The subject is a female aged 40–49, the lesion involves the arm, the photograph was taken at an angle: 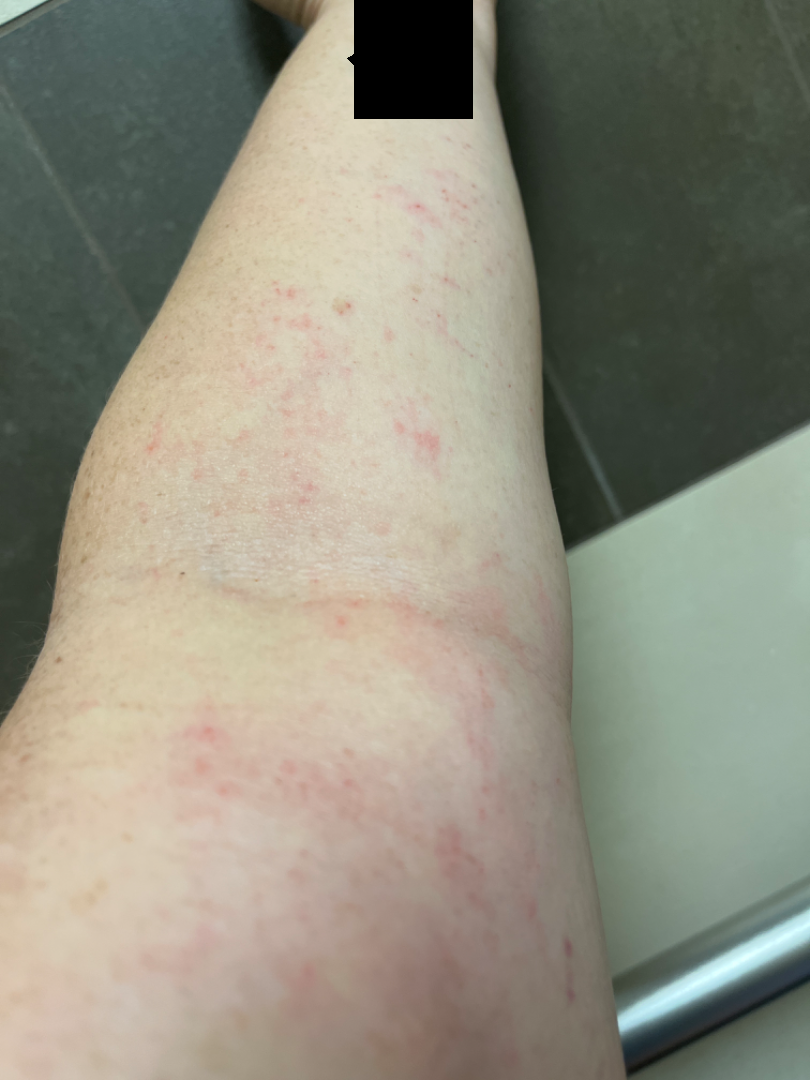systemic symptoms — none reported | patient-reported symptoms — itching, bothersome appearance and burning | self-categorized as — skin that appeared healthy to them | history — less than one week | texture — raised or bumpy | dermatologist impression — Acute dermatitis, NOS and Irritant Contact Dermatitis were considered with similar weight; also raised was Eczema; with consideration of Allergic Contact Dermatitis.